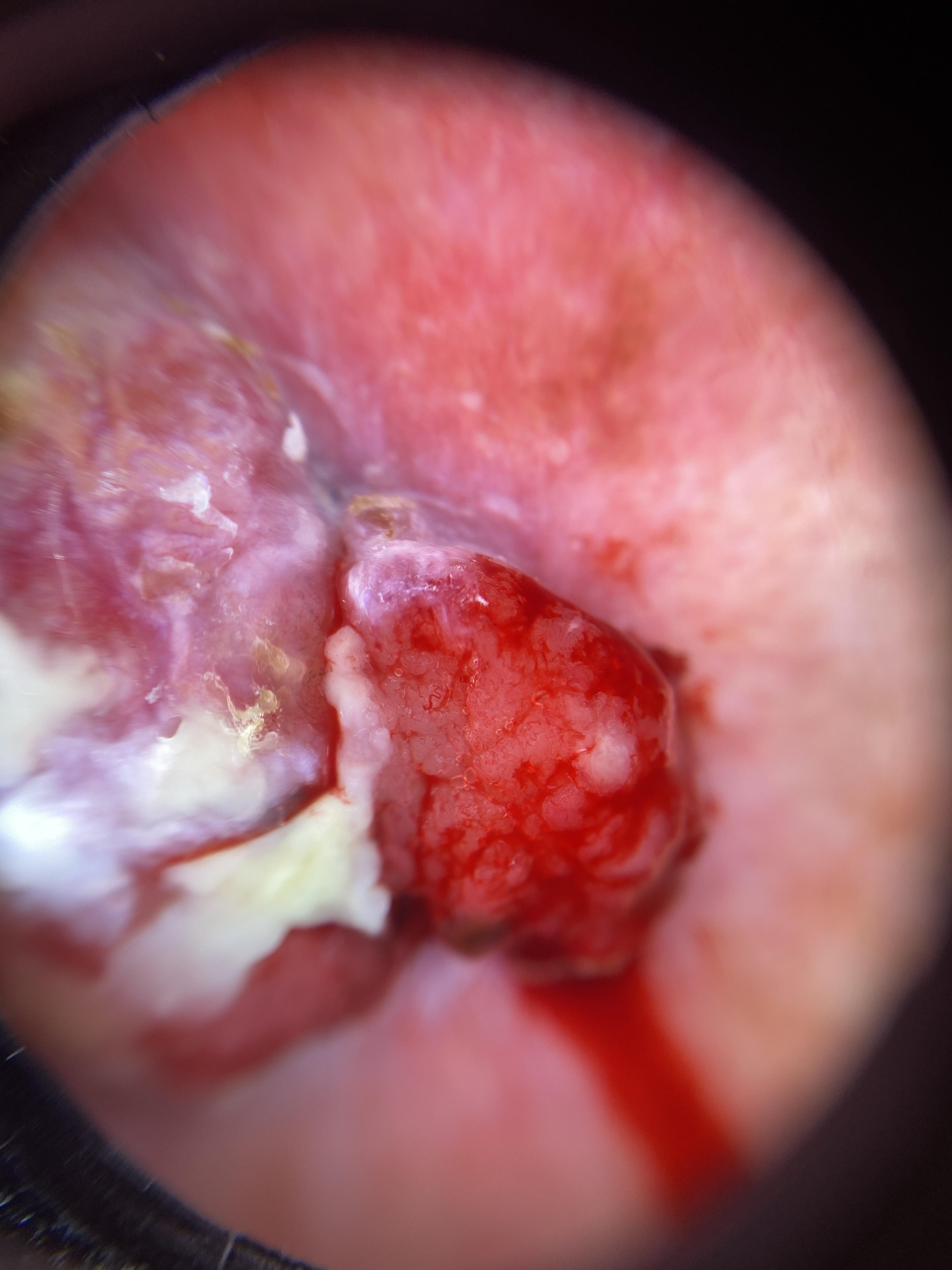Case summary:
The chart documents a previous melanoma. The patient was assessed as Fitzpatrick phototype II. A male subject in their mid- to late 80s or older. A dermoscopic close-up of a skin lesion. Located on the trunk (the posterior trunk).
Diagnosis:
Confirmed on histopathology as a melanoma.